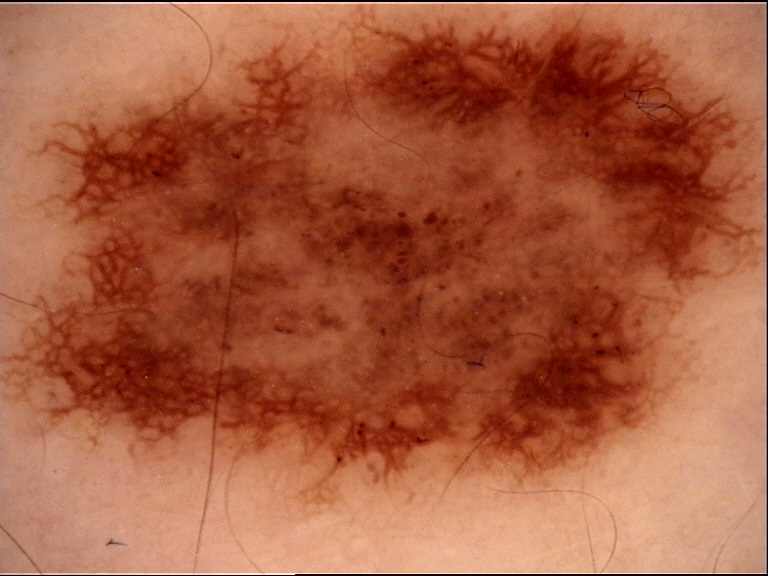– diagnostic label: dysplastic junctional nevus (expert consensus)